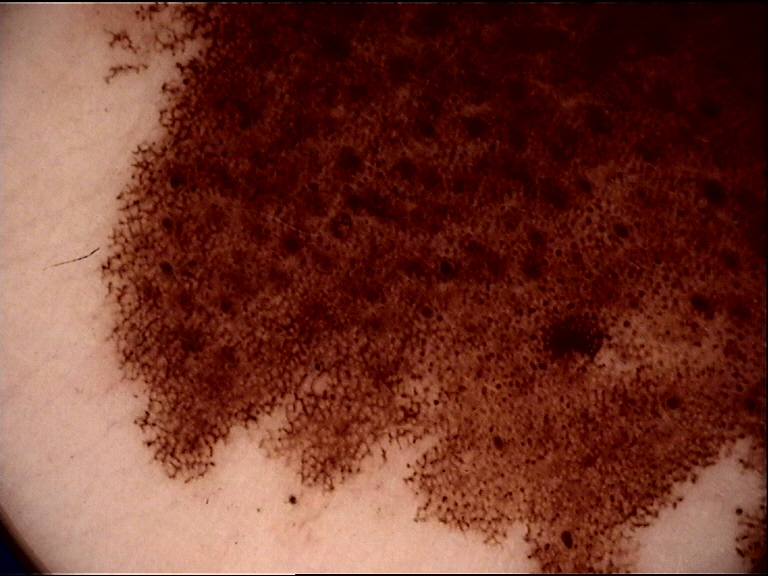A dermatoscopic image of a skin lesion.
The morphology is that of a banal lesion.
Classified as a congenital compound nevus.